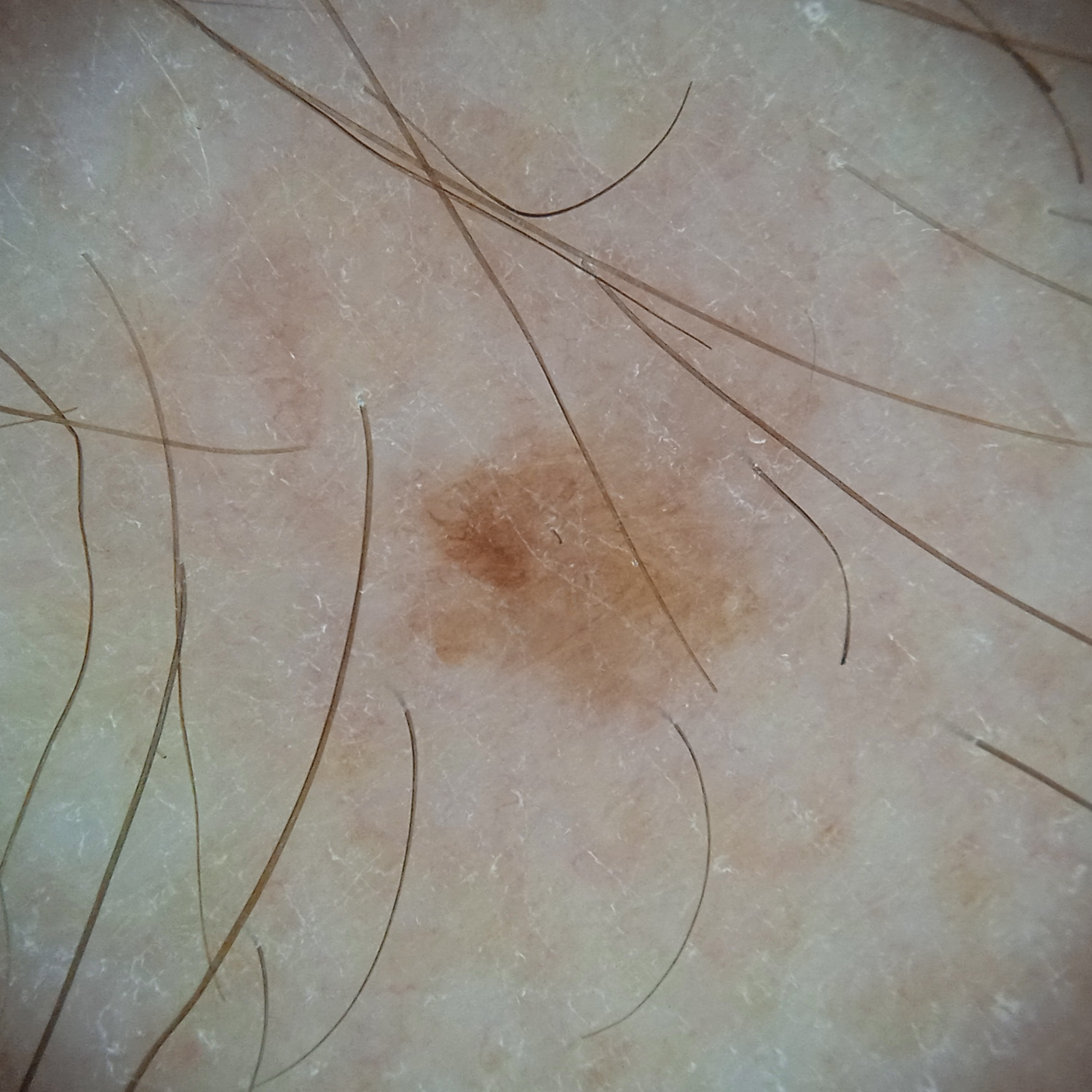Dermatologist review favored a seborrheic keratosis.